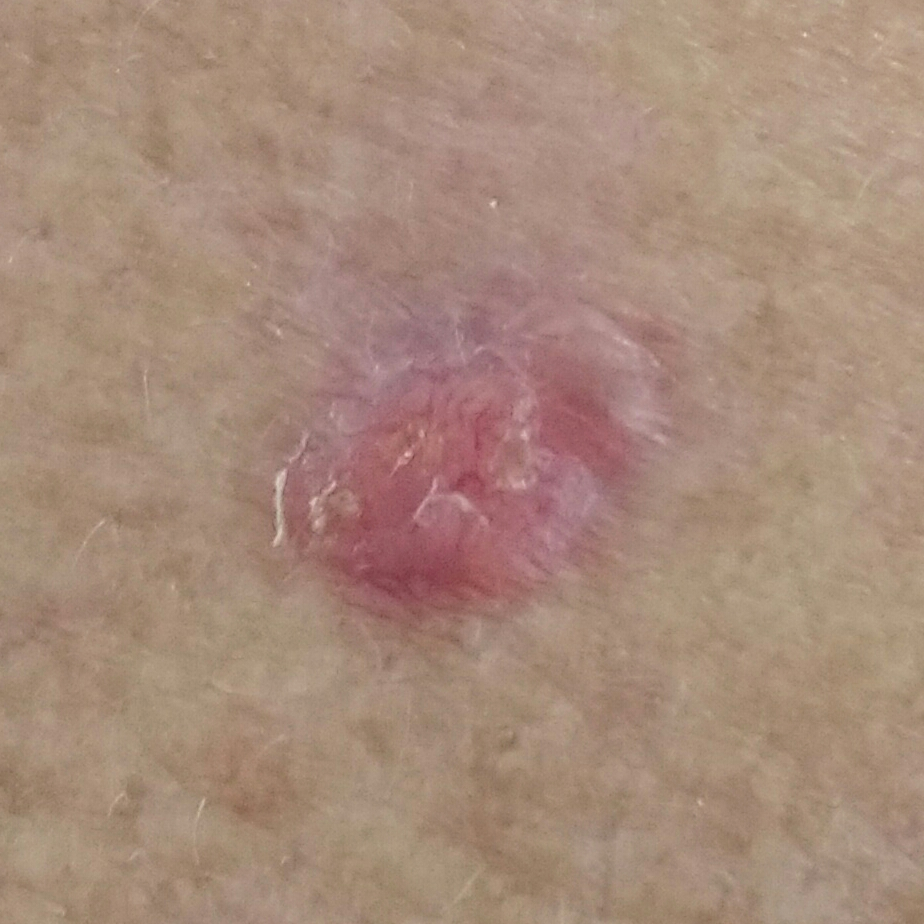The patient is skin type II. A male patient 64 years of age. The chart records pesticide exposure and prior skin cancer (patient or family). A clinical photo of a skin lesion taken with a smartphone. Located on the back. Measuring about 10 × 9 mm. The patient reports that the lesion has bled, itches, has grown, and is elevated. Biopsy-confirmed as a skin cancer — a basal cell carcinoma.